Dermoscopy of a skin lesion:
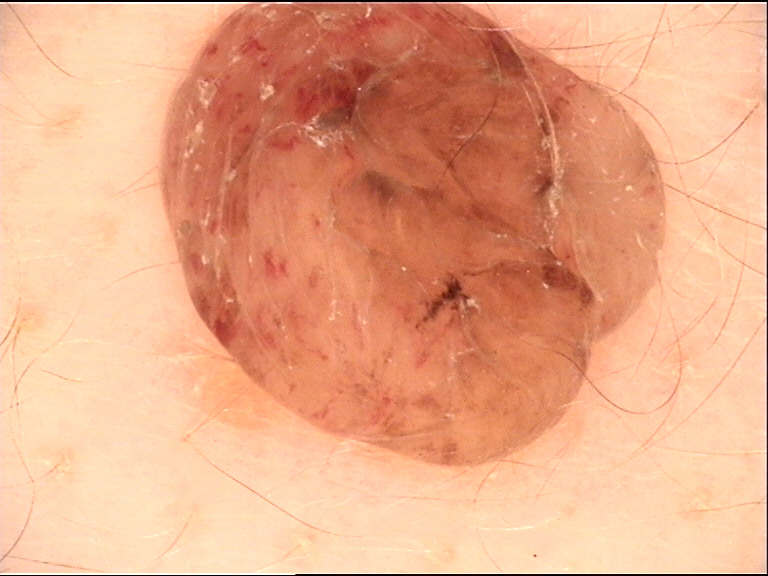classification = banal
class = dermal nevus (expert consensus)